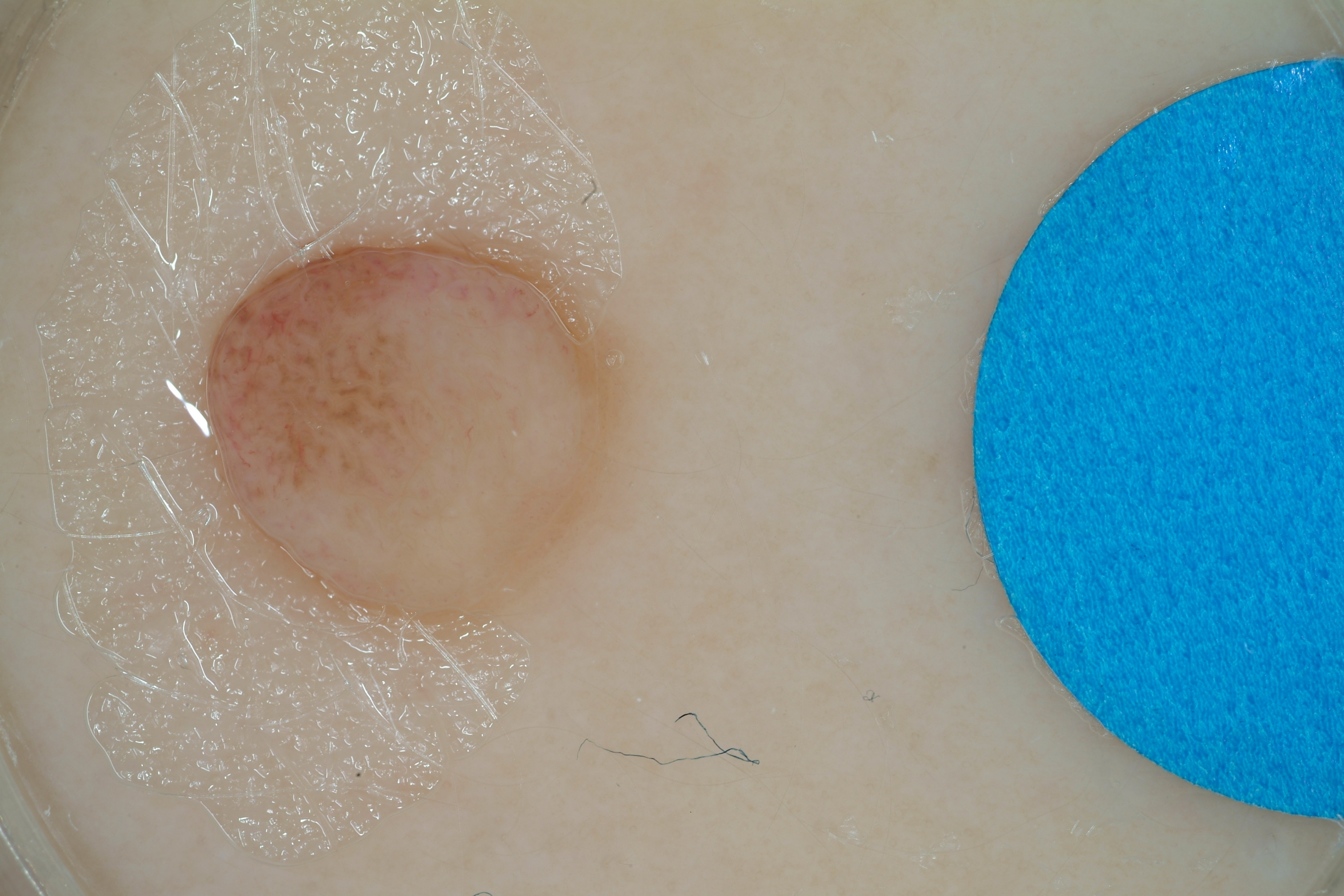image = dermatoscopic image of a skin lesion | dermoscopic features not present = negative network, streaks, pigment network, milia-like cysts, and globules | lesion location = x1=206 y1=249 x2=611 y2=613 | diagnostic label = a melanocytic nevus, a benign lesion.